Dermoscopy of a skin lesion — 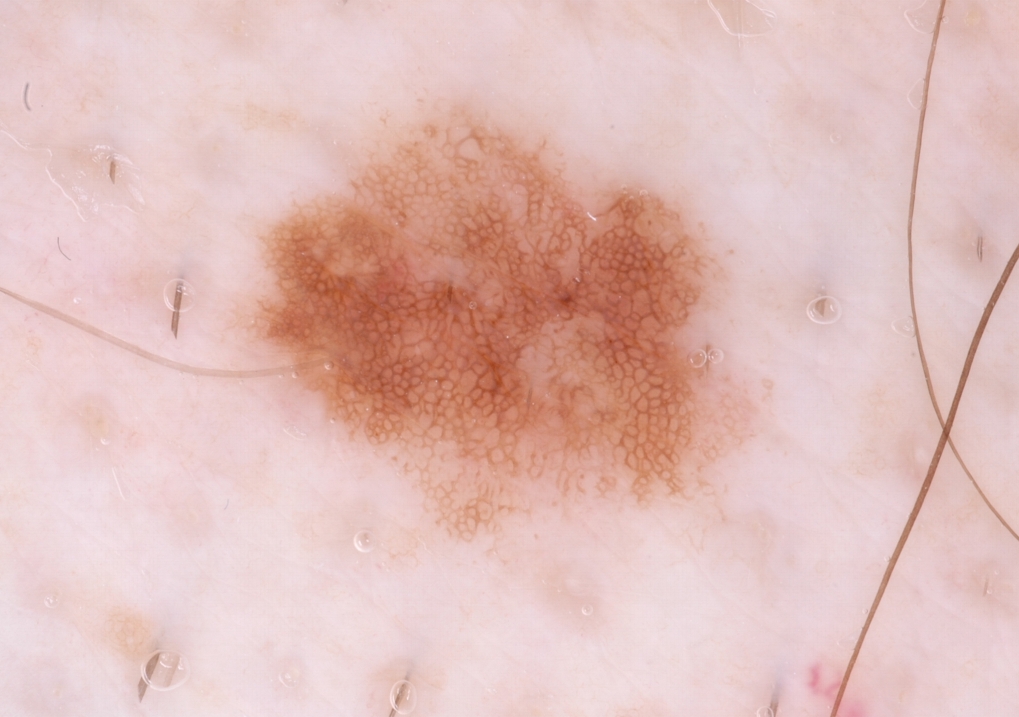The lesion occupies roughly 19% of the field. The lesion spans x1=242 y1=106 x2=746 y2=531. Dermoscopically, the lesion shows pigment network; no streaks, milia-like cysts, negative network, or globules. Diagnosed as a melanocytic nevus, a benign skin lesion.